Dermoscopy of a skin lesion — 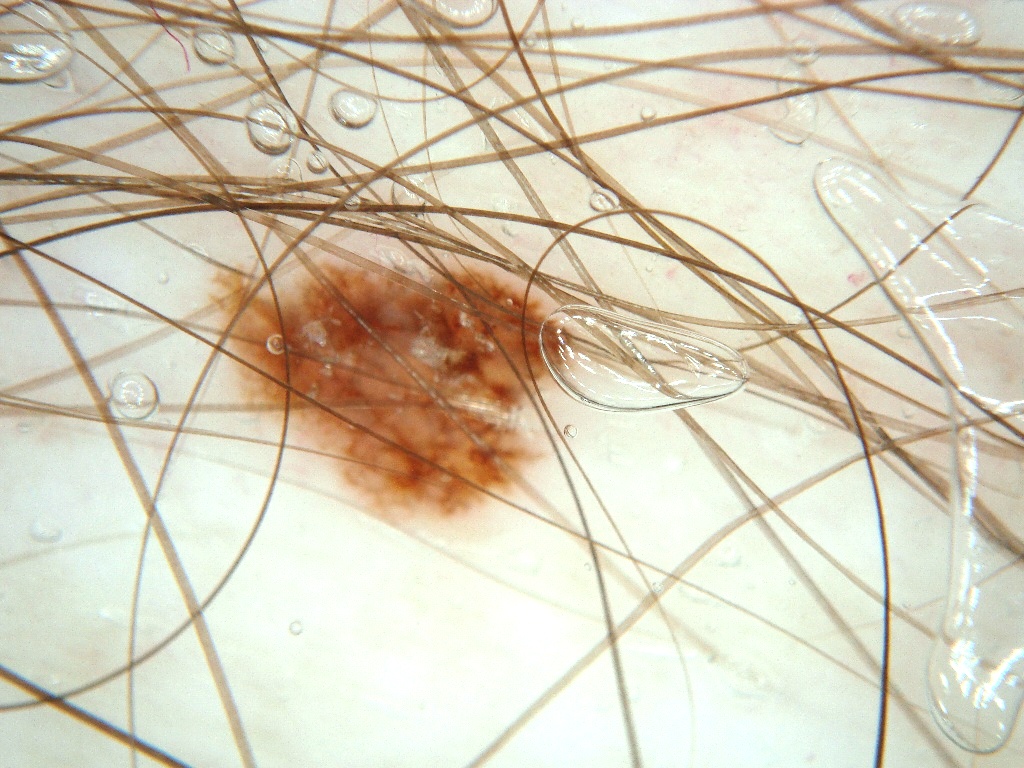The lesion covers approximately 12% of the dermoscopic field.
The lesion occupies the region <box>191, 229, 587, 544</box>.
Diagnosed as a benign lesion.